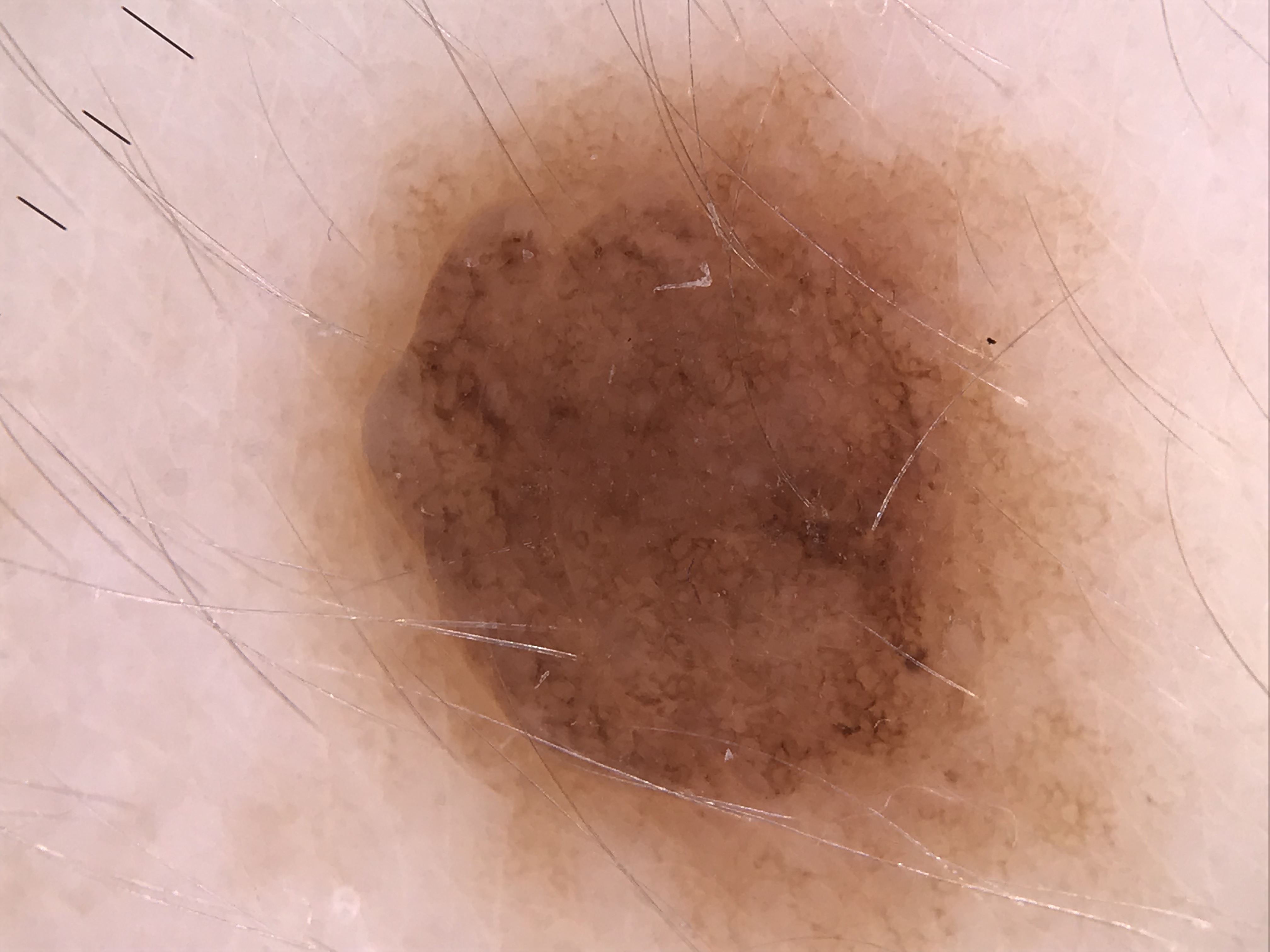Case:
A dermatoscopic image of a skin lesion. This is a banal lesion.
Impression:
The diagnosis was a compound nevus.